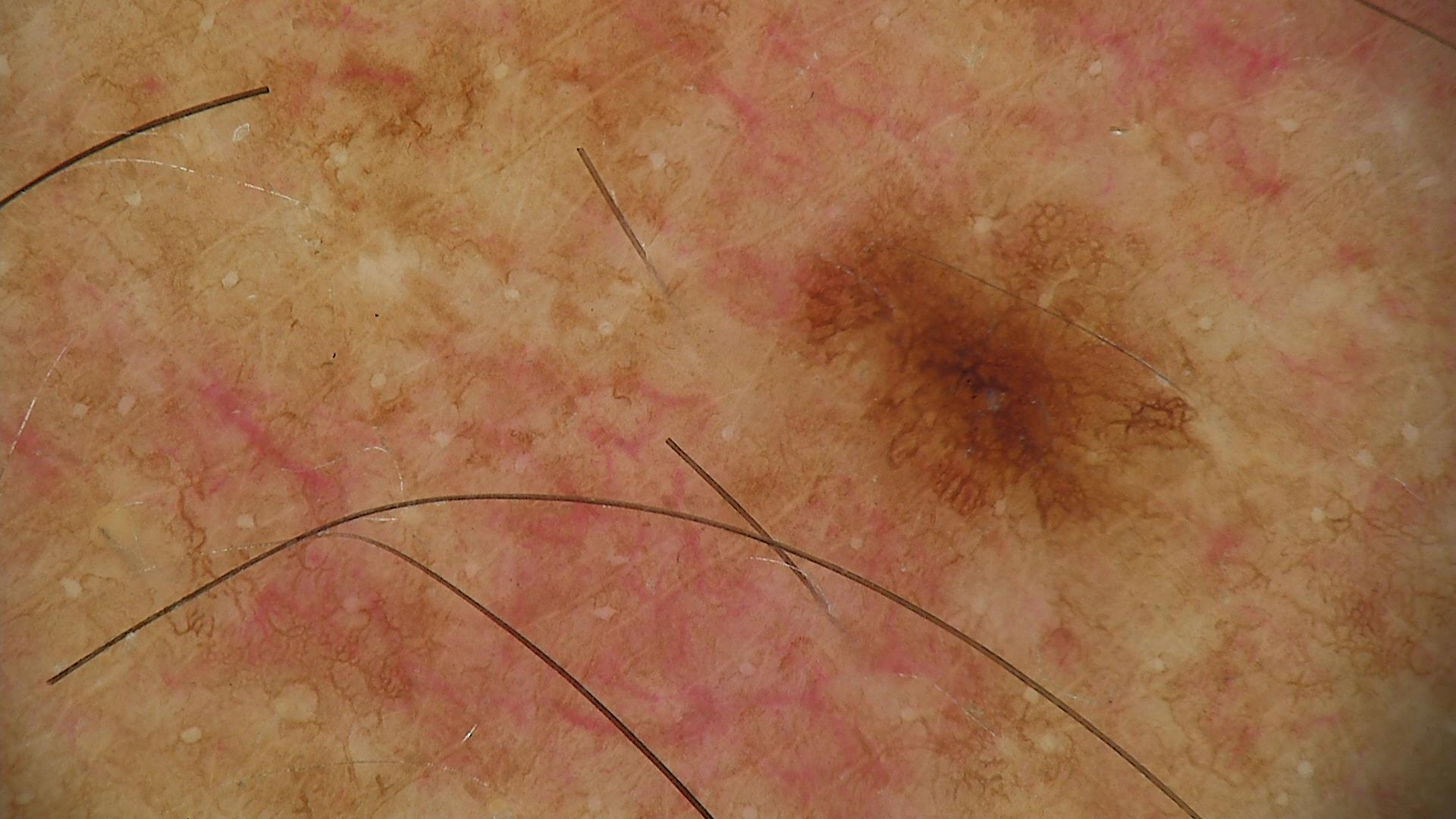Diagnosed as a dysplastic junctional nevus.